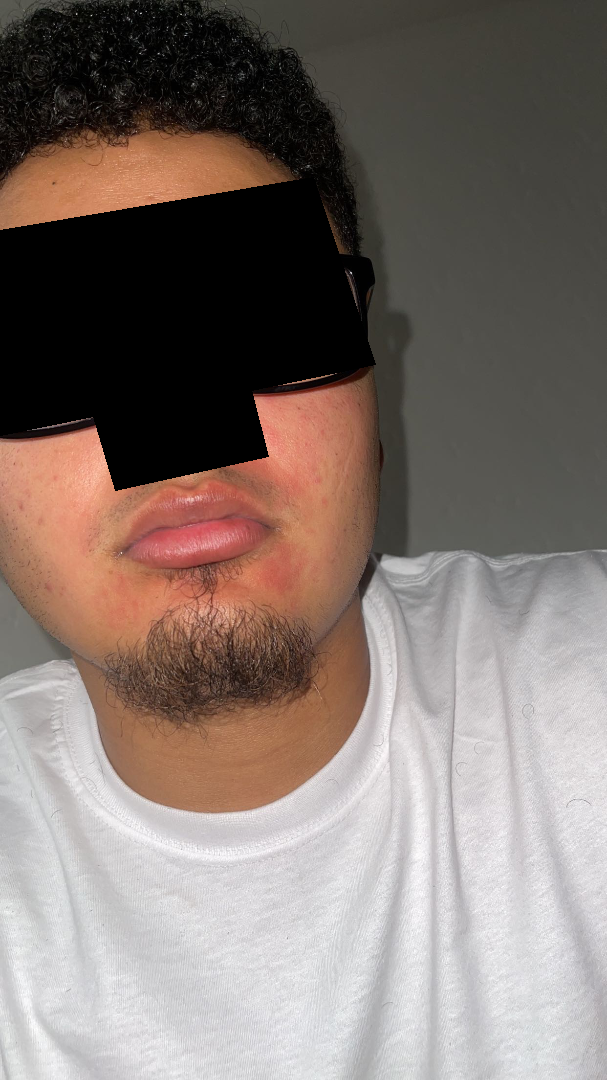The lesion involves the head or neck. The patient indicates bothersome appearance. The photograph was taken at a distance. The patient described the issue as a rash. Fitzpatrick III. Acne, Rosacea and Perioral Dermatitis were considered with similar weight.